The patient is Fitzpatrick II · the chart documents a previous melanoma · a male patient aged approximately 65 — 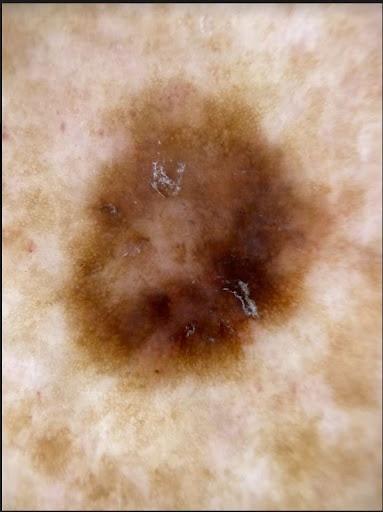On biopsy, the diagnosis was a melanoma.